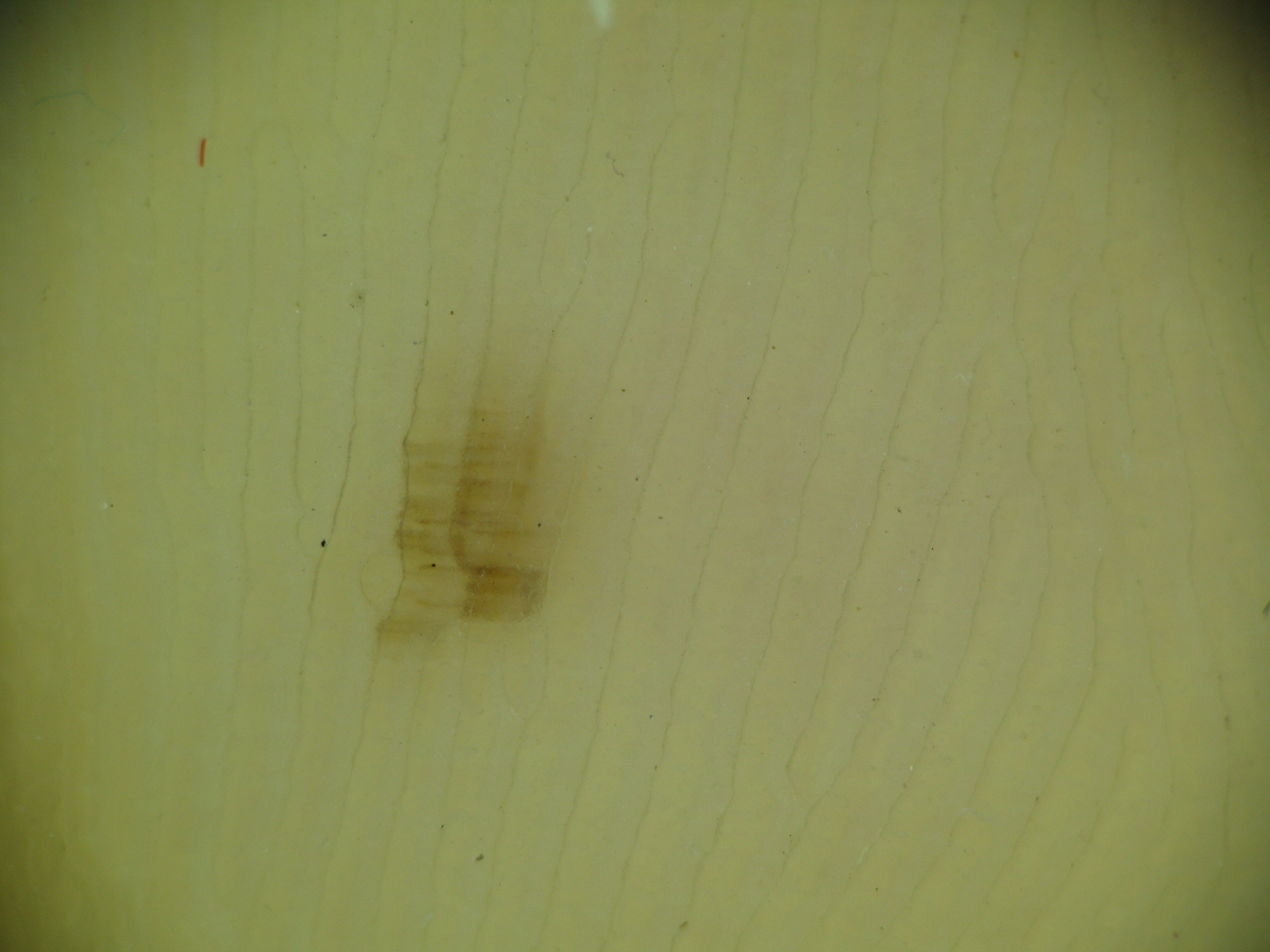Case:
A dermatoscopic image of a skin lesion.
Impression:
Labeled as a banal lesion — an acral junctional nevus.